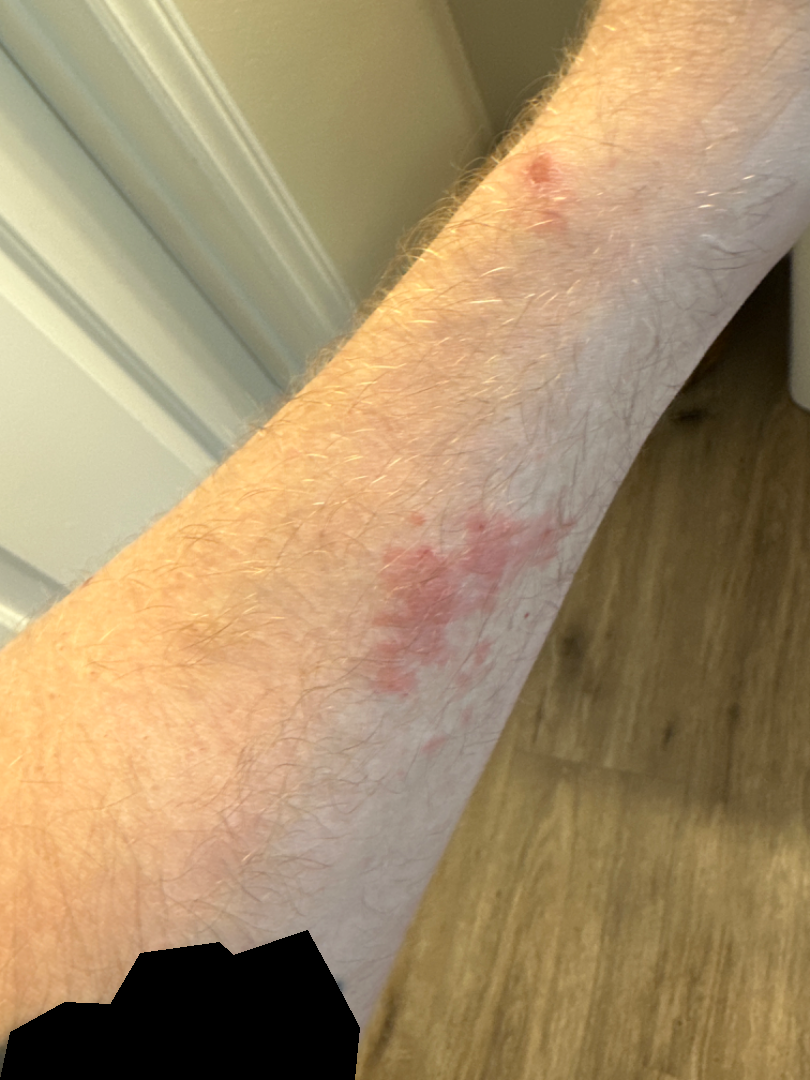assessment — not assessable
self-categorized as — a rash
site — arm
lesion symptoms — bothersome appearance and itching
view — at an angle
surface texture — flat
symptom duration — less than one week